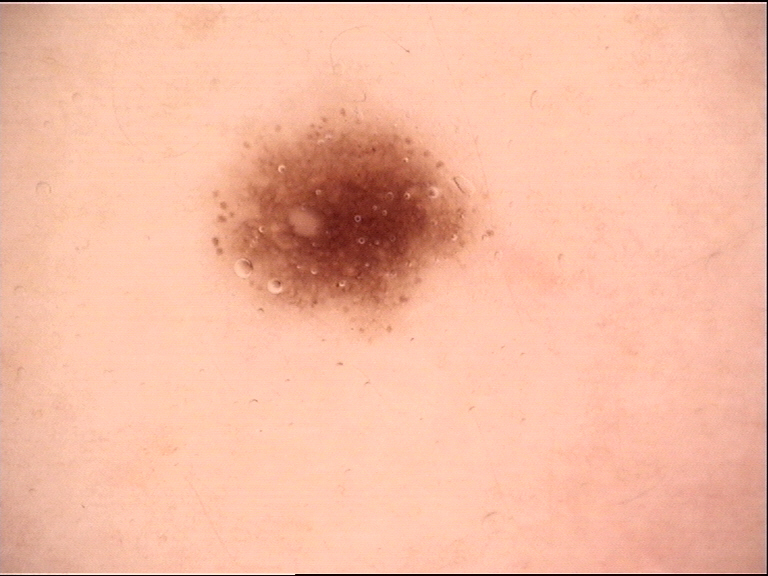The diagnosis was a dysplastic junctional nevus.